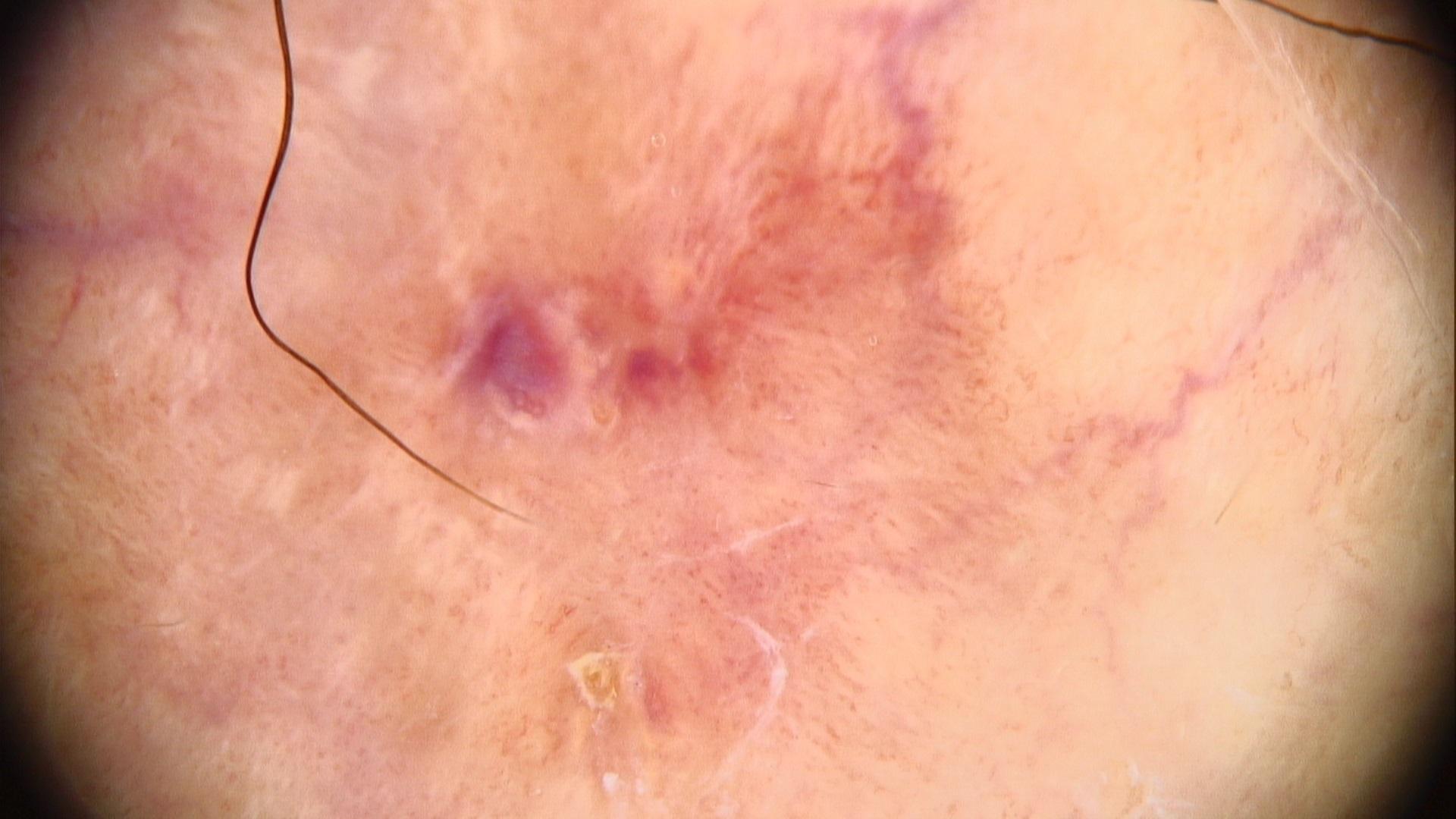<case>
<patient>
<age_approx>70</age_approx>
<sex>female</sex>
</patient>
<lesion_location>
<region>a lower extremity</region>
</lesion_location>
<diagnosis>
<name>Squamous cell carcinoma</name>
<malignancy>malignant</malignancy>
<confirmation>histopathology</confirmation>
<lineage>epidermal</lineage>
</diagnosis>
</case>